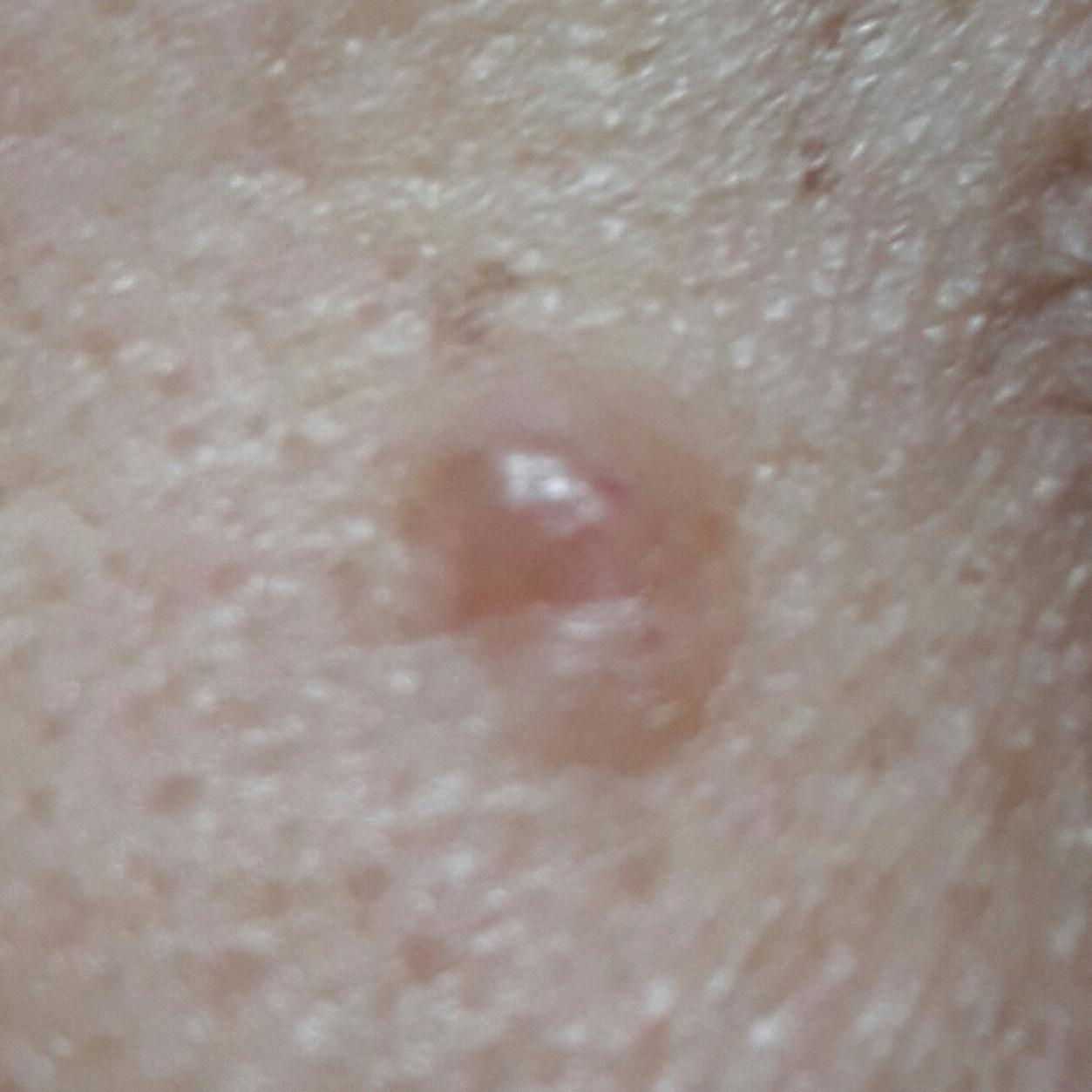patient — female, age 62
image type — smartphone clinical photo
skin type — III
exposures — prior malignancy (patient or family)
location — the nose
lesion diameter — approx. 6 × 4 mm
patient-reported symptoms — growth, elevation
pathology — basal cell carcinoma (biopsy-proven)